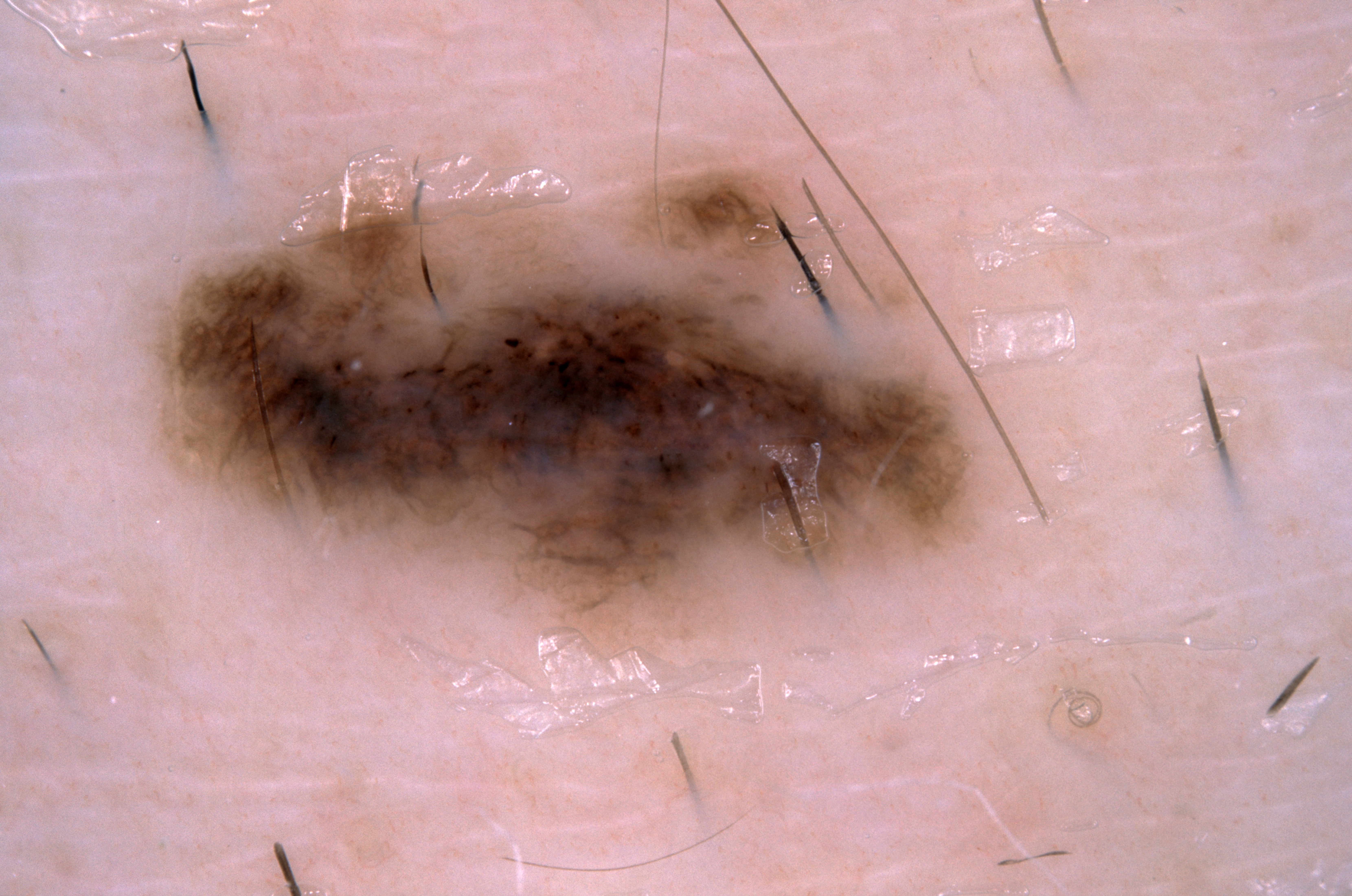A dermoscopic image of a skin lesion. The patient is a male in their mid- to late 50s. The lesion takes up about 34% of the image. On dermoscopy, the lesion shows pigment network. With coordinates (x1, y1, x2, y2), the lesion is bounded by 125 147 1070 698. Consistent with a melanocytic nevus.